A female subject aged 33-37. A contact-polarized dermoscopy image of a skin lesion.
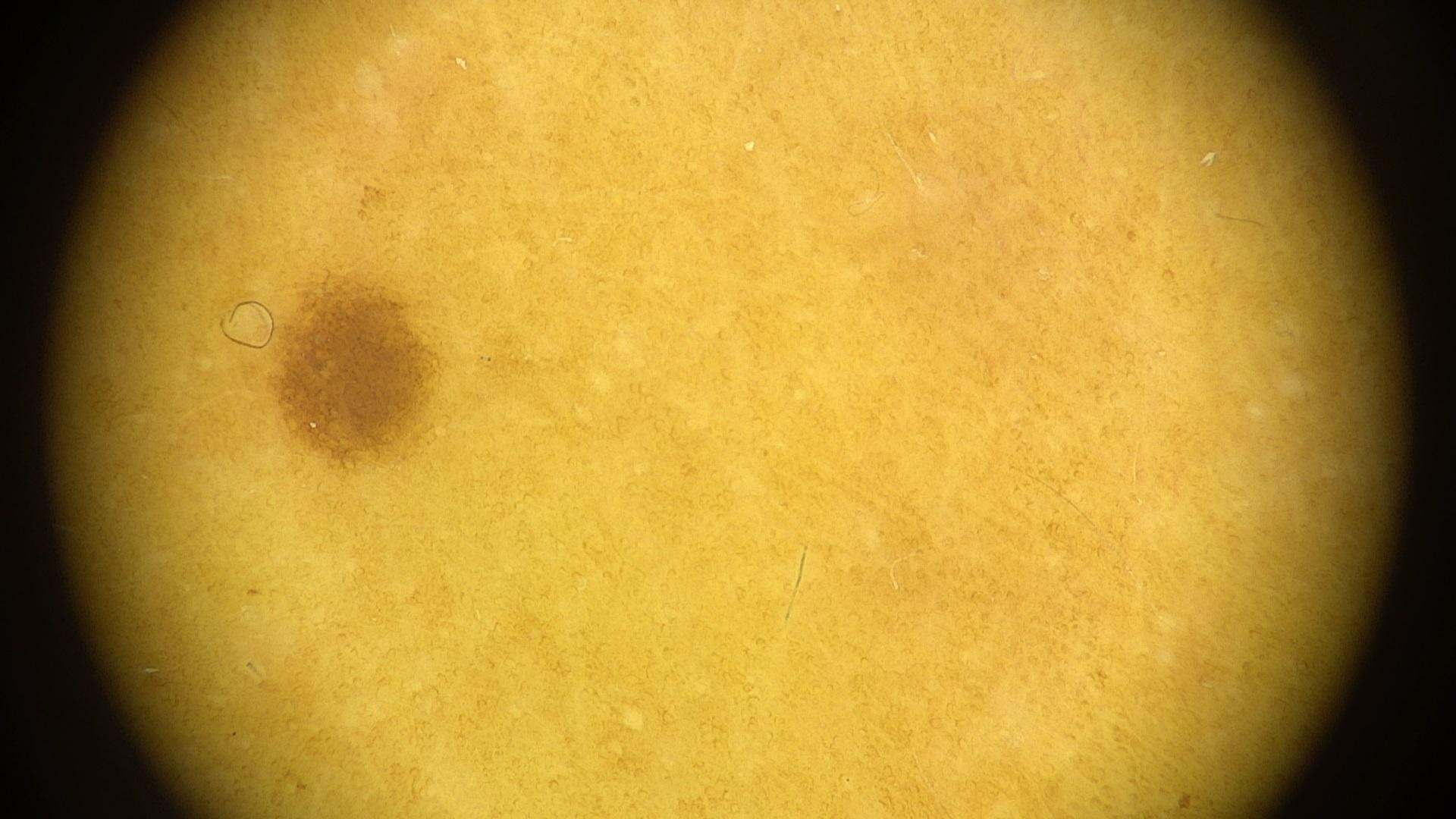The lesion is on an upper extremity. Consistent with a nevus.